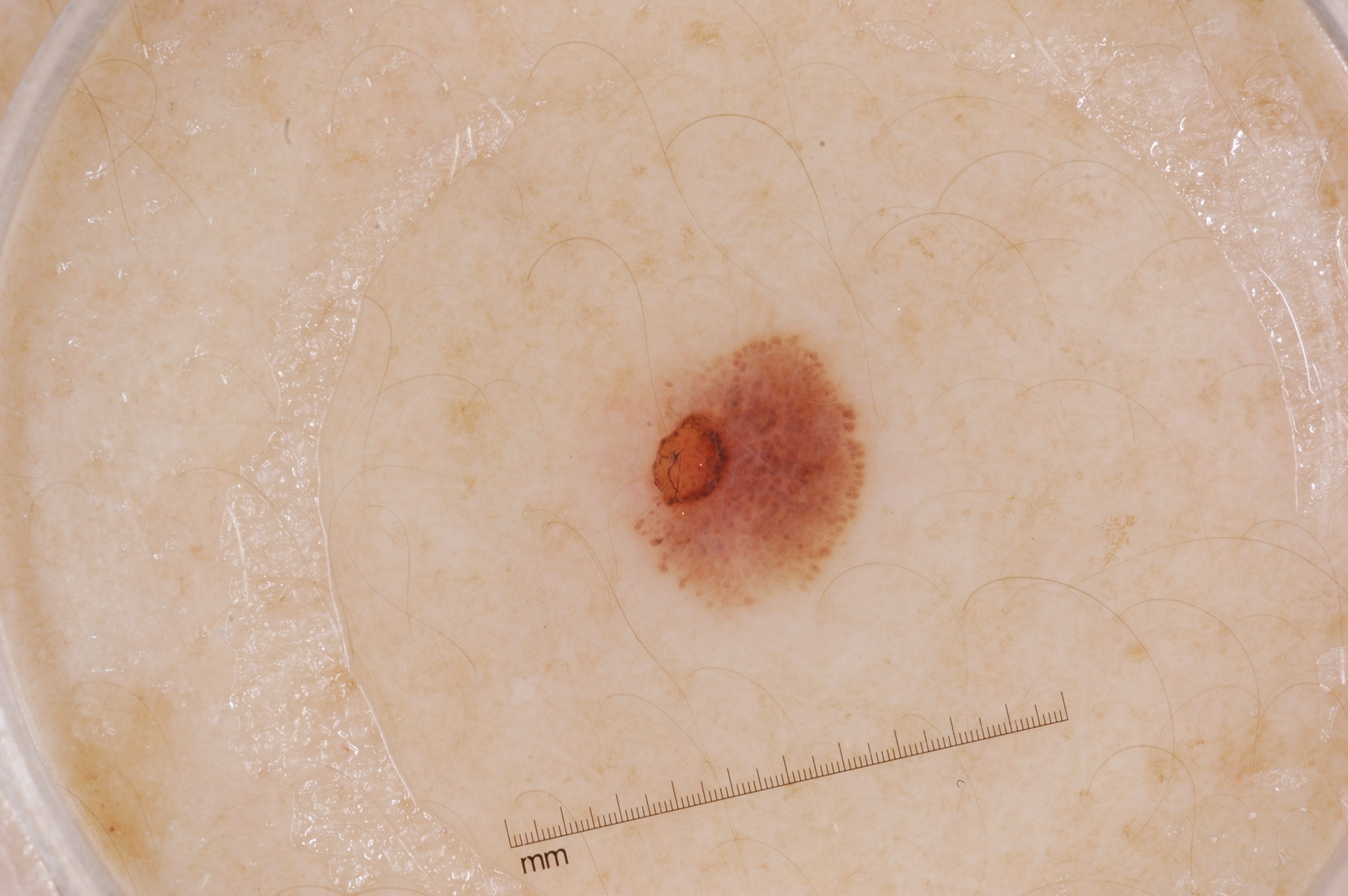Q: How was this image acquired?
A: dermoscopy
Q: Patient demographics?
A: female, aged 38 to 42
Q: What does dermoscopy show?
A: streaks and negative network
Q: Where is the lesion located?
A: bbox=[622, 336, 863, 602]
Q: Lesion extent?
A: small
Q: What did the assessment conclude?
A: a melanocytic nevus, a benign skin lesion